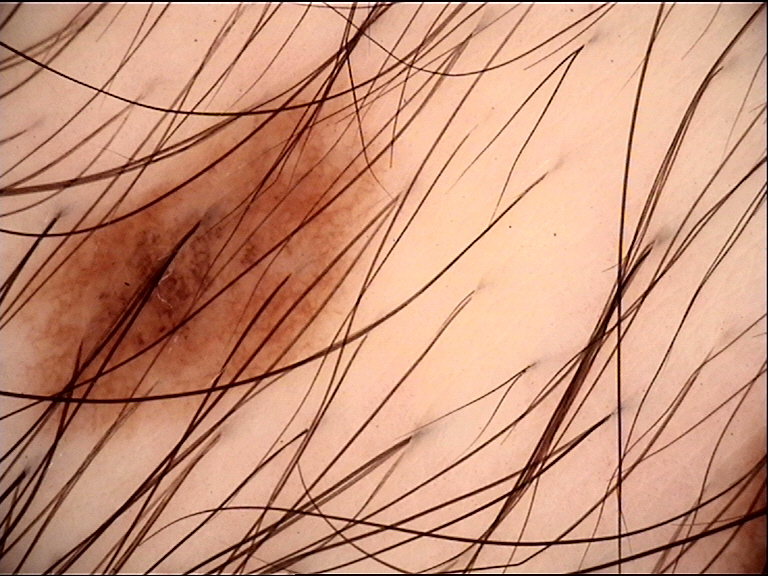diagnosis: dysplastic junctional nevus (expert consensus).